Dermoscopy of a skin lesion.
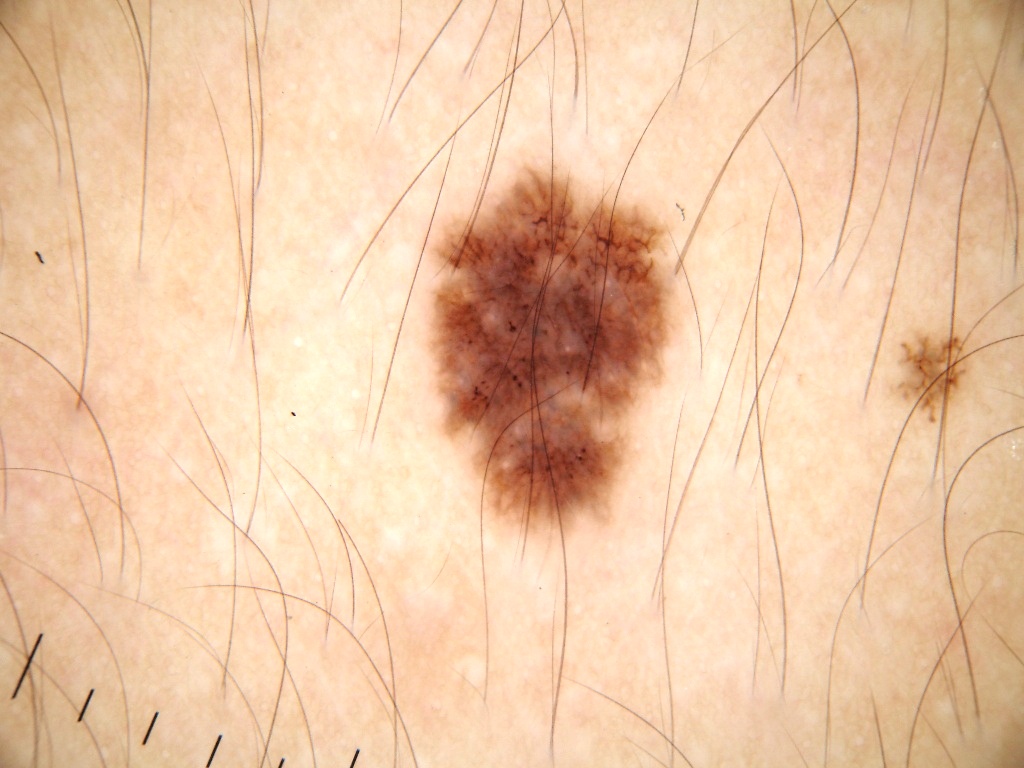Findings: Dermoscopic review identifies pigment network, globules, streaks, and milia-like cysts; no negative network. In (x1, y1, x2, y2) order, the visible lesion spans 431 169 669 530. Impression: Clinically diagnosed as a melanocytic nevus, a benign lesion.